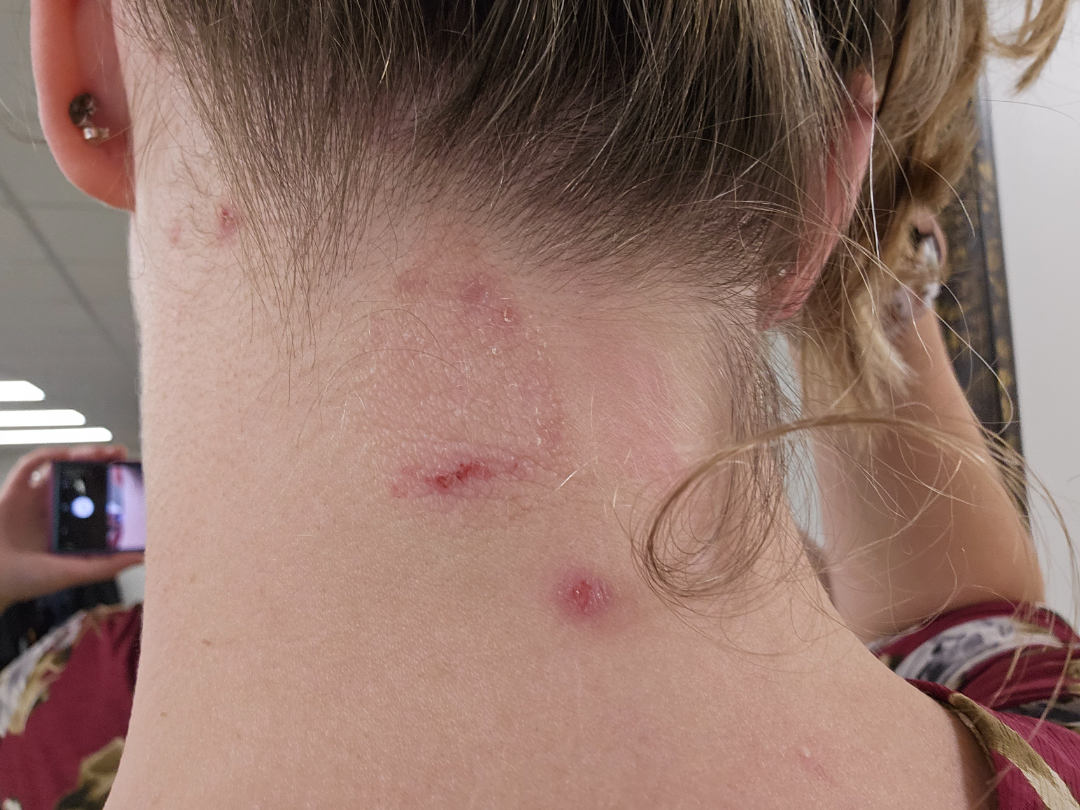Notes:
- described texture · rough or flaky
- lesion symptoms · bleeding and itching
- body site · head or neck
- shot type · at an angle
- impression · the differential, in no particular order, includes Psoriasis, Eczema and Lichen Simplex Chronicus